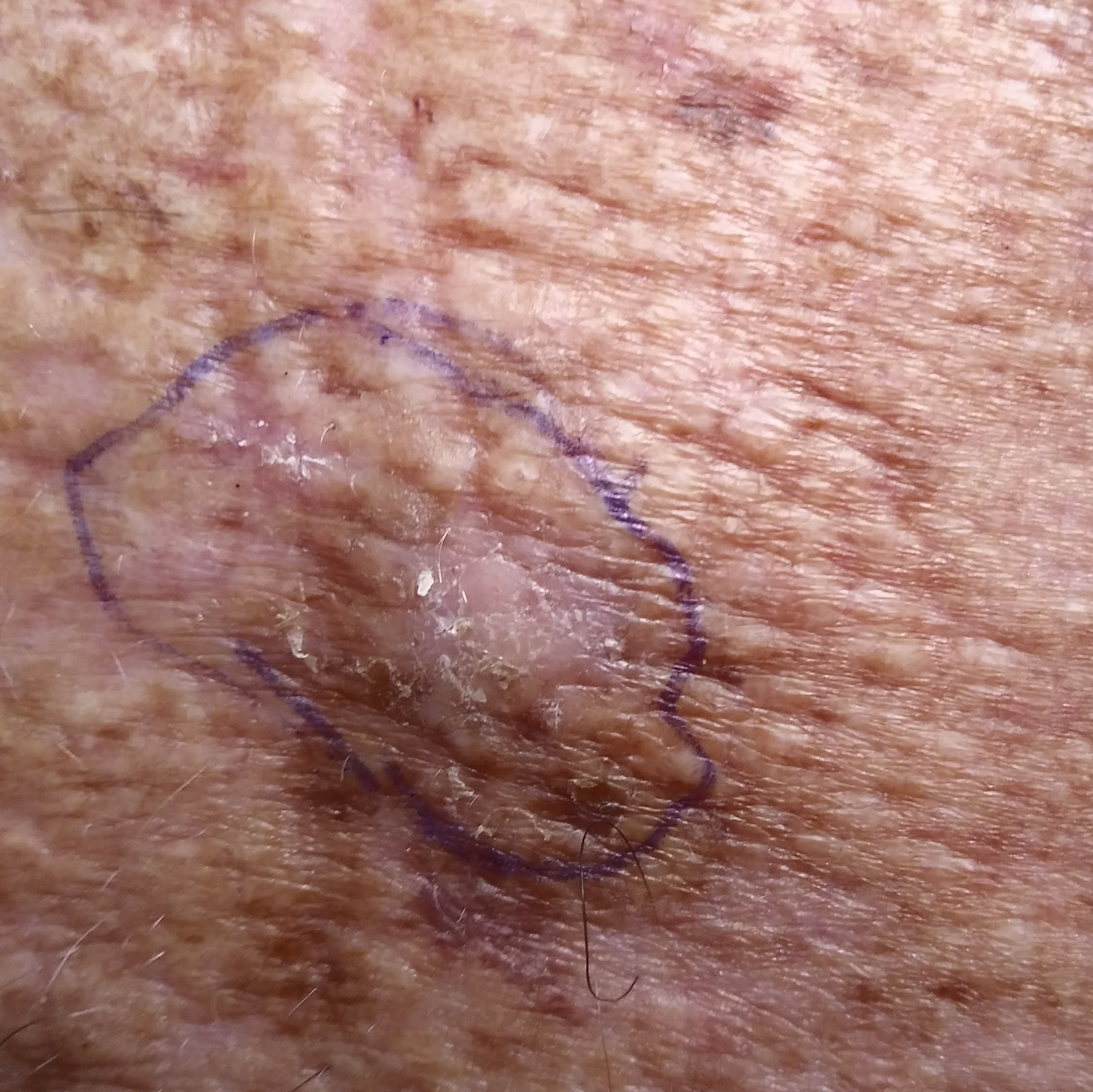image = clinical photo, subject = aged 79, body site = the chest, assessment = actinic keratosis (clinical consensus).